A female subject aged 38-42, dermoscopy of a skin lesion.
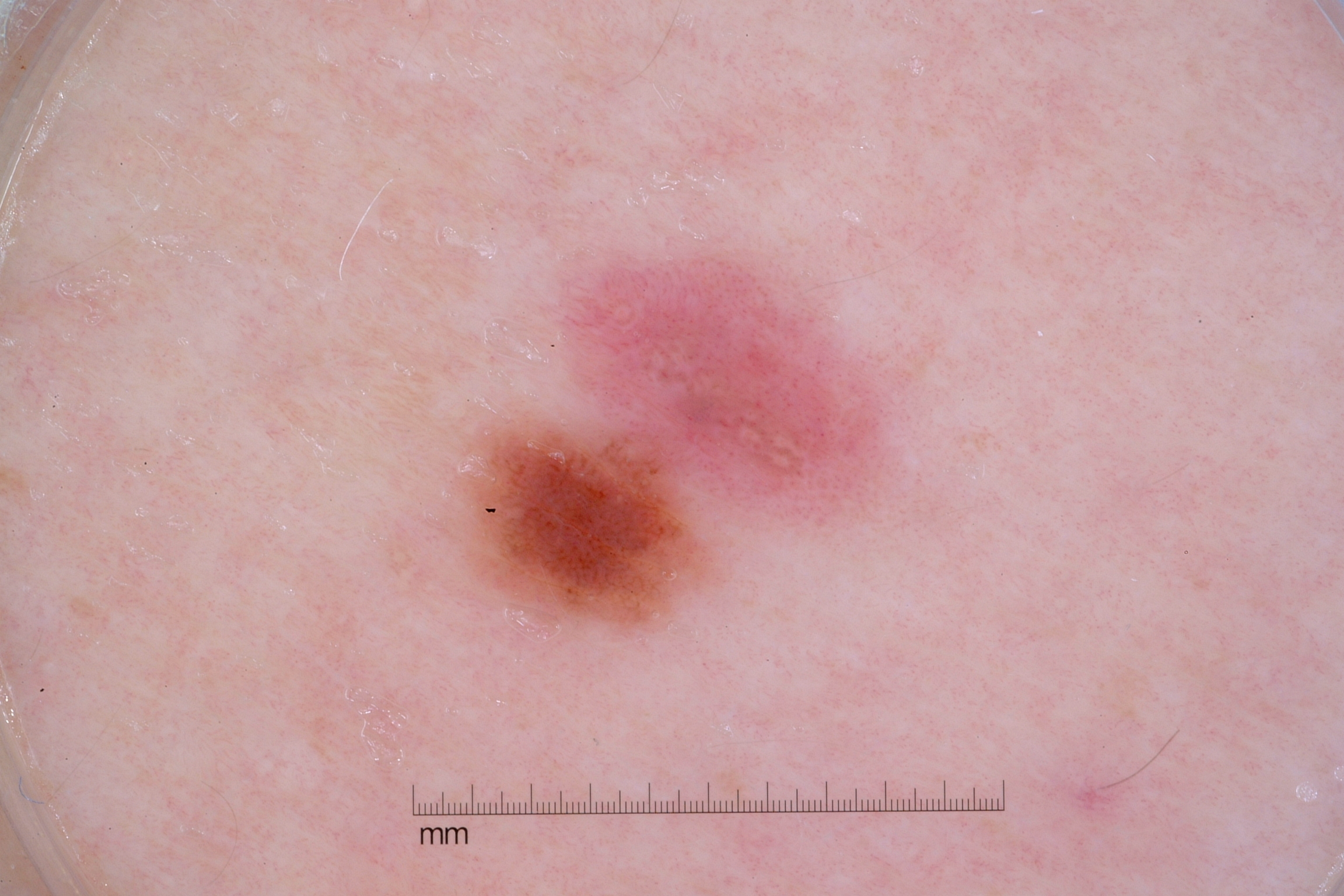lesion bbox = (462, 260, 881, 630)
features = negative network; absent: streaks, pigment network, and milia-like cysts
impression = a melanocytic nevus